A dermoscopic image of a skin lesion.
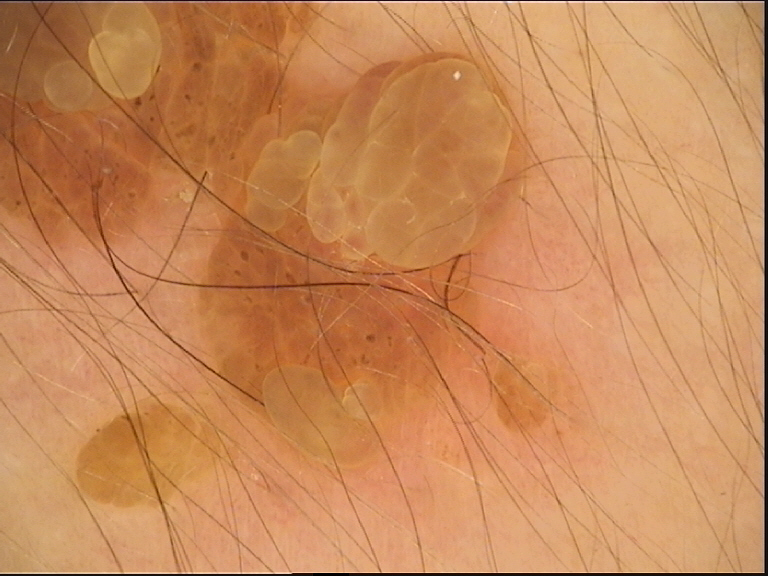Impression:
Labeled as a keratinocytic lesion — a seborrheic keratosis.